A skin lesion imaged with a dermatoscope.
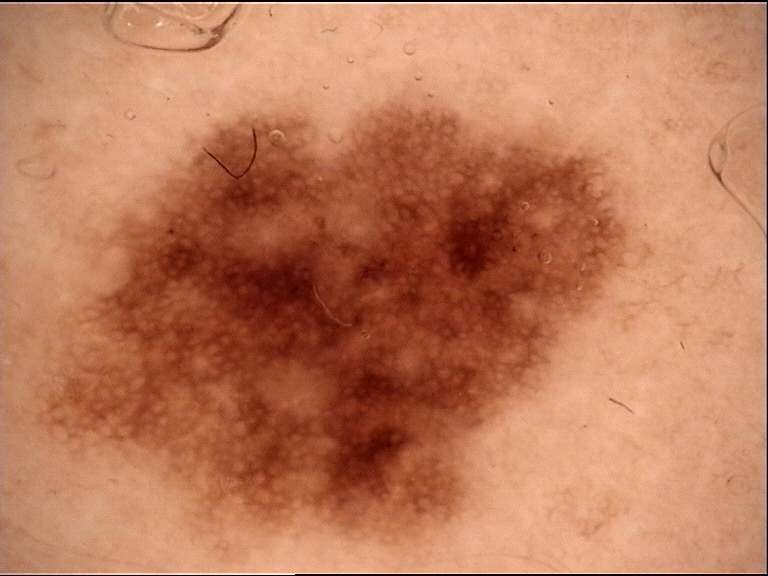assessment: dysplastic junctional nevus (expert consensus).